Close-up view; the subject is a male aged 40–49; the affected area is the leg and arm — 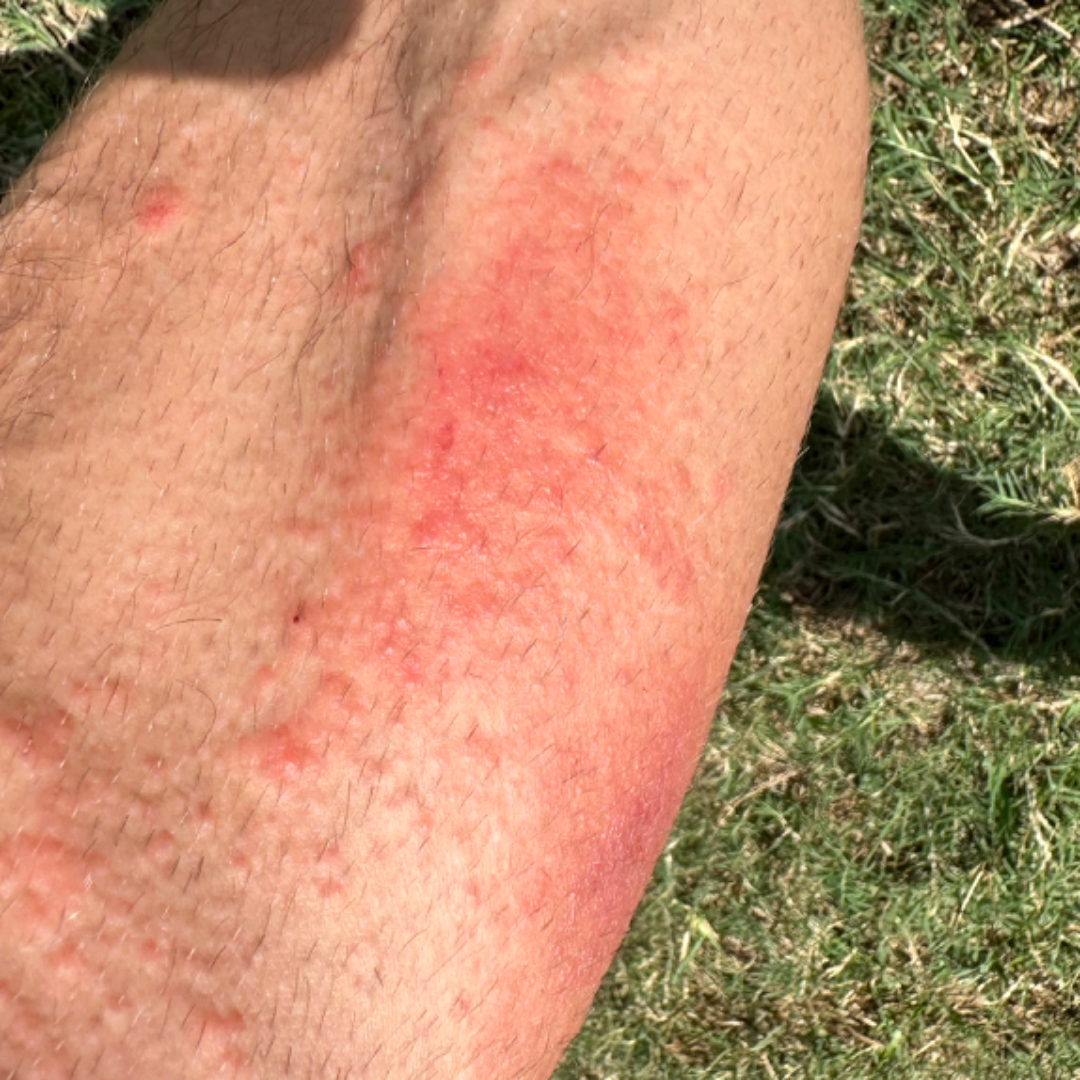Assessment: The condition could not be reliably identified from the image. Clinical context: The patient notes enlargement, bothersome appearance and itching. Present for less than one week. The patient notes the lesion is raised or bumpy. The patient described the issue as a rash. Fitzpatrick III; non-clinician graders estimated Monk skin tone scale 3 or 4. The patient reported no systemic symptoms.